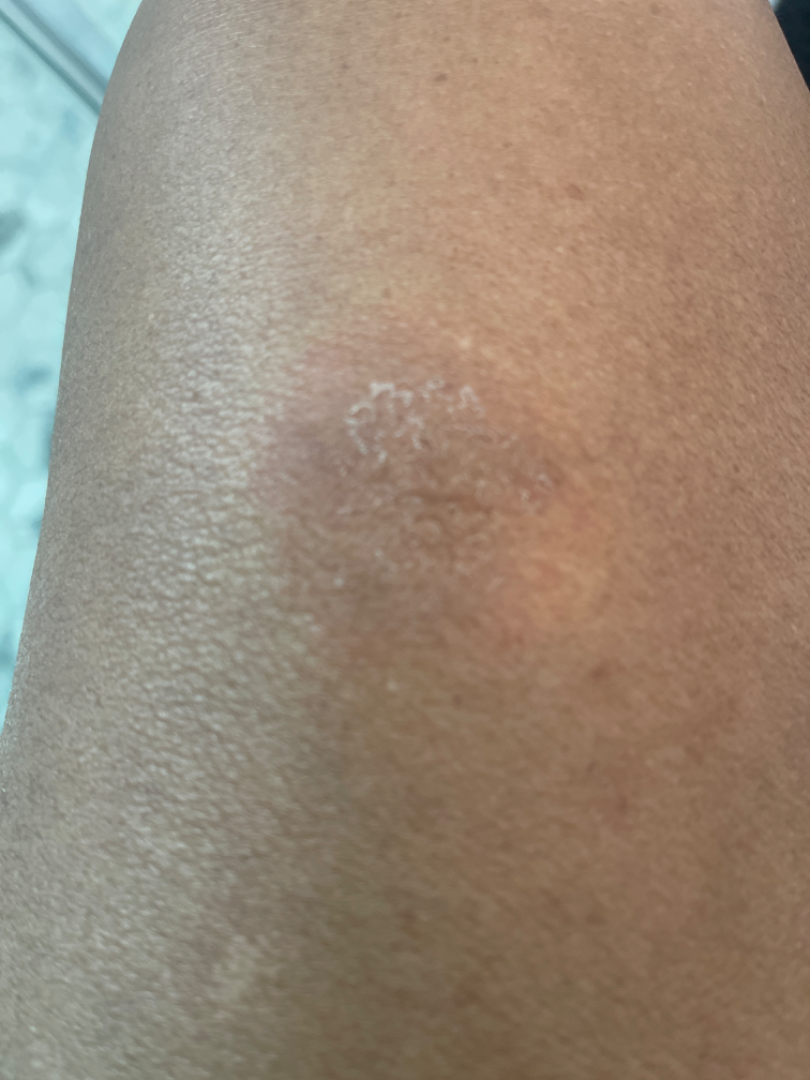dermatologist impression: the differential includes Eczema, Impetigo and Psoriasis, with no clear leading consideration.